The patient also reports fatigue. The condition has been present for one to four weeks. The photograph is a close-up of the affected area. Female contributor, age 40–49. Self-categorized by the patient as a rash. Skin tone: Fitzpatrick phototype II. The affected area is the arm. Texture is reported as fluid-filled and raised or bumpy — 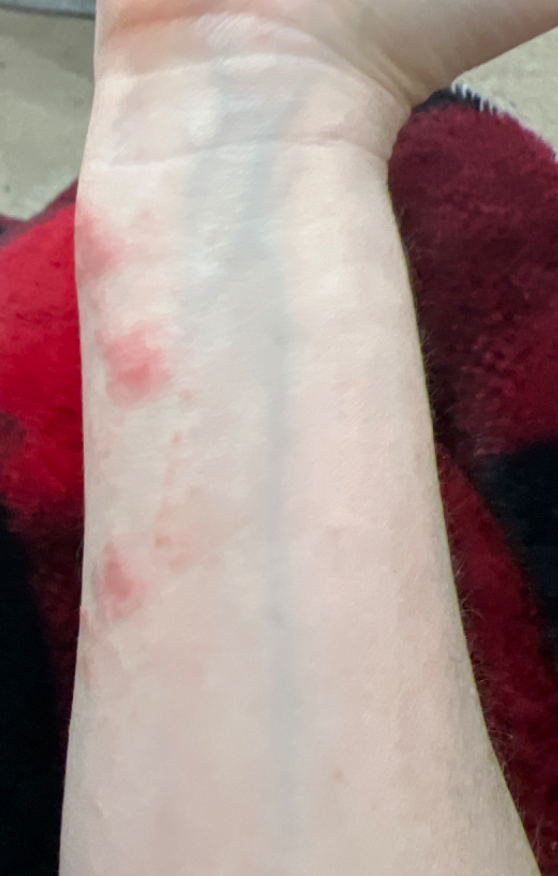Three independent reviewers: favoring Allergic Contact Dermatitis; also raised was Insect Bite; a more distant consideration is Phytophotodermatitis; less likely is Eczema.